A dermoscopic image of a skin lesion.
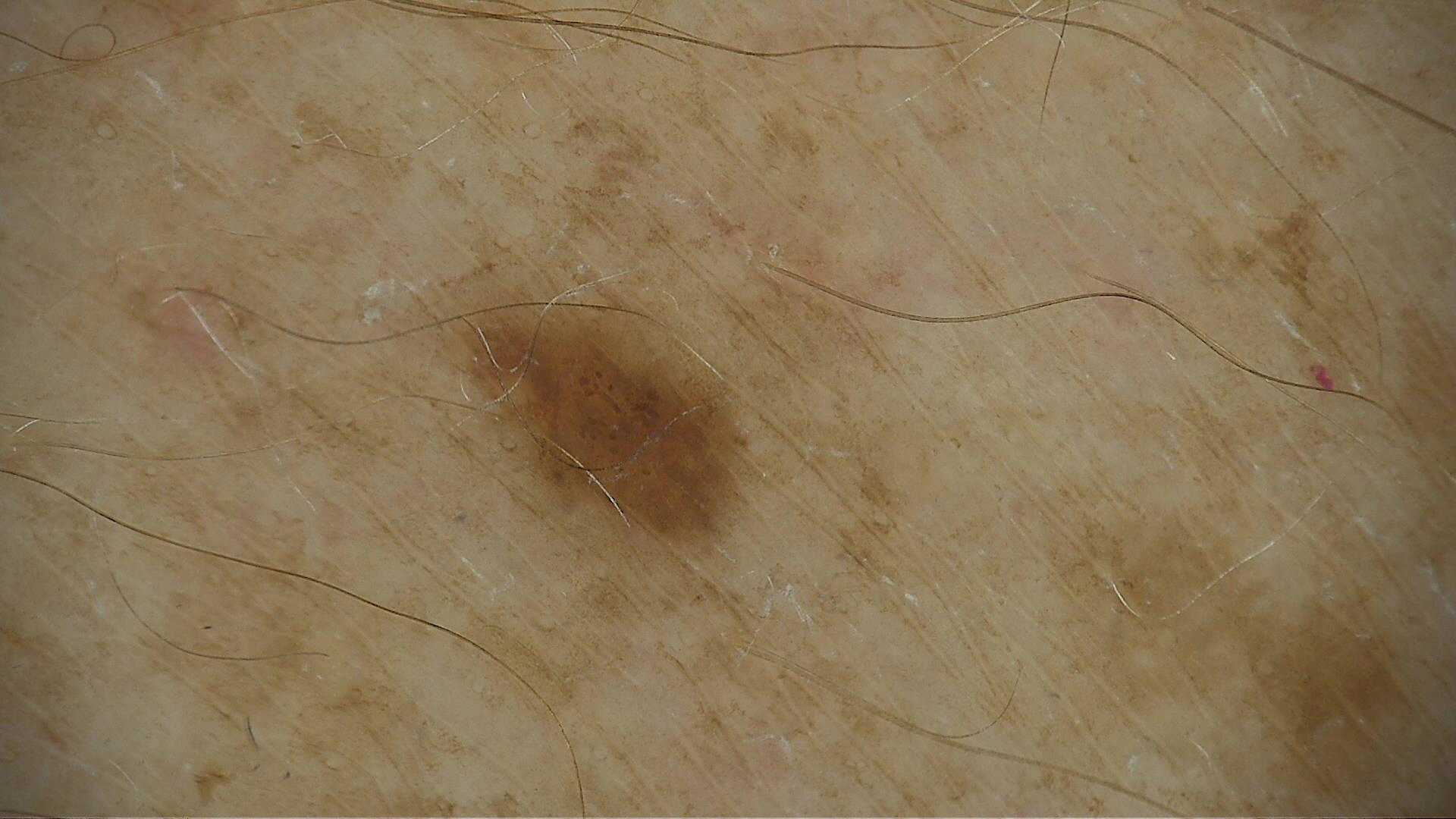Conclusion: The diagnostic label was a benign lesion — a dysplastic junctional nevus.